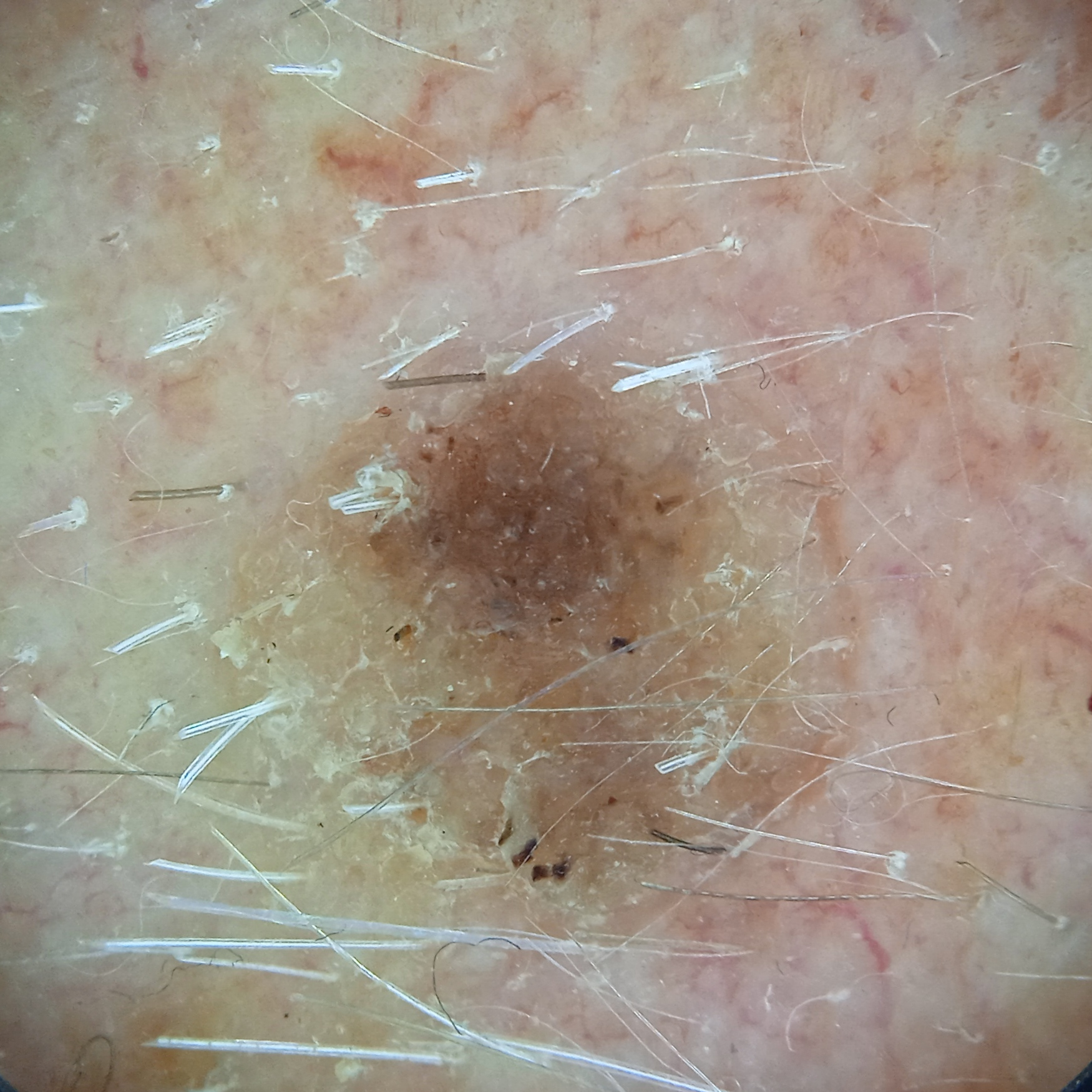Impression: The dermatologists' assessment was a seborrheic keratosis.